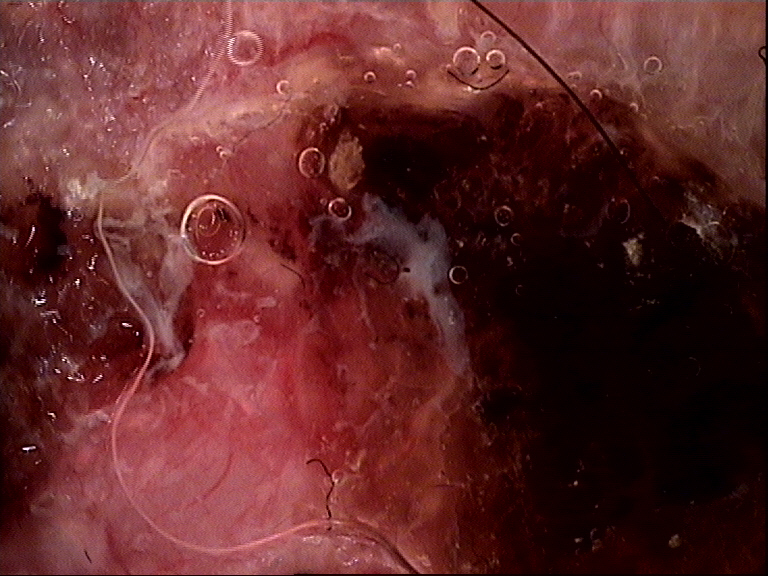The biopsy diagnosis was a squamous cell carcinoma.